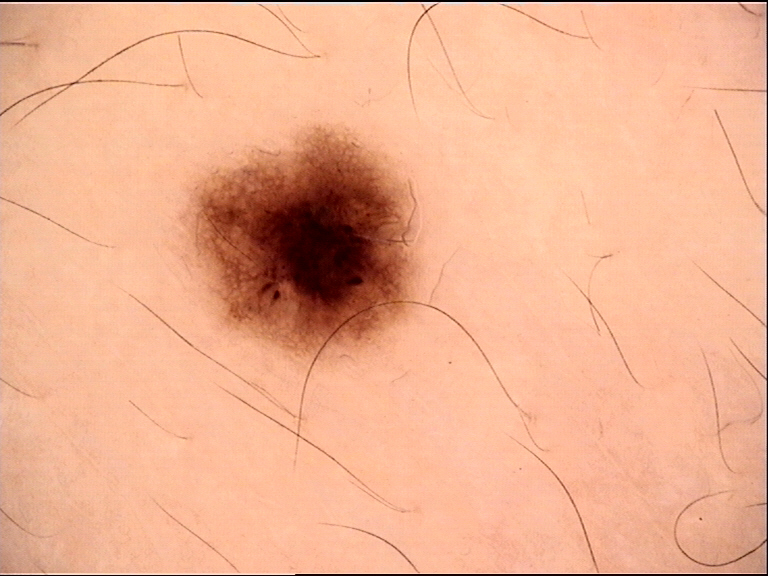modality — dermoscopy
assessment — dysplastic junctional nevus (expert consensus)